Located on the arm, the photograph is a close-up of the affected area — 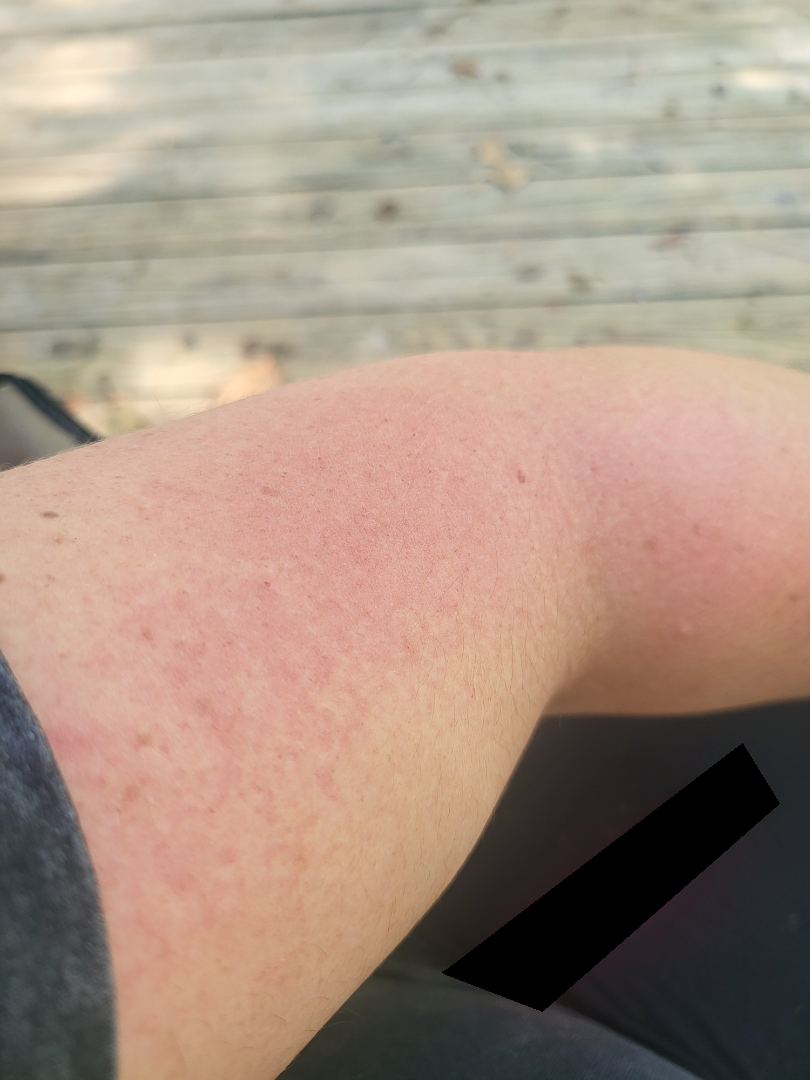clinical impression: consistent with Acute dermatitis, NOS